The patient says their skin reddens painfully with sun exposure. A female patient 81 years of age. A dermoscopy image of a skin lesion.
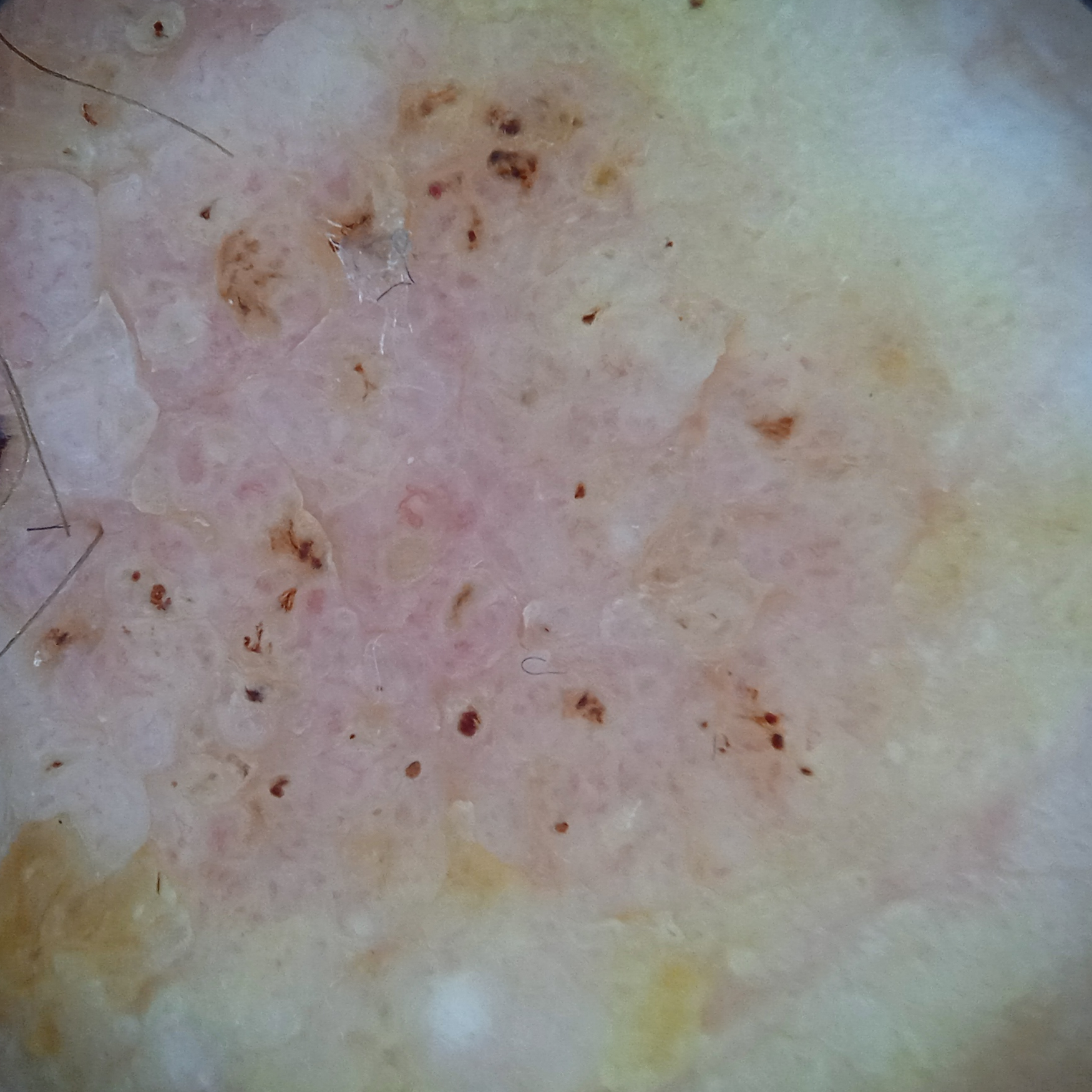body site=the face; diagnostic label=seborrheic keratosis (dermatologist consensus).